The patient considered this a rash · located on the arm · the subject is male · reported lesion symptoms include burning and itching · an image taken at a distance · reported duration is about one day: 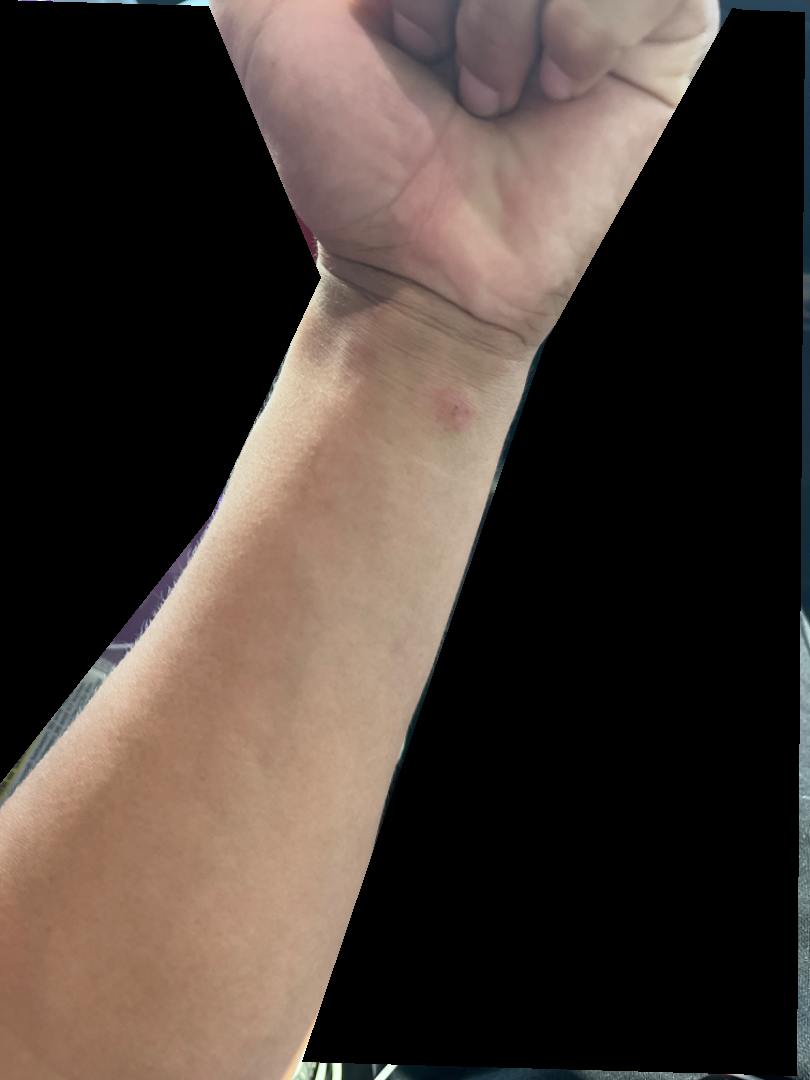differential: favoring Insect Bite; also raised was Abrasion, scrape, or scab; possibly Allergic Contact Dermatitis